The subject is 40–49, female; the photo was captured at an angle; the affected area is the top or side of the foot: 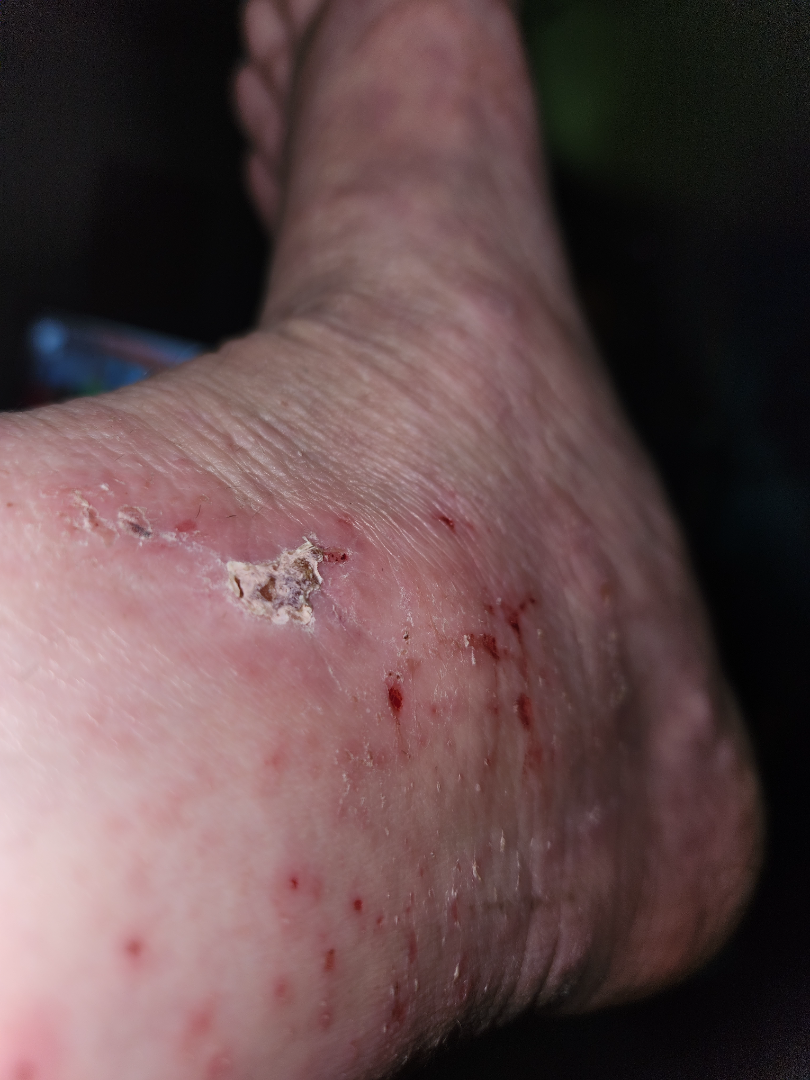Assessment: The skin condition could not be confidently assessed from this image.